No relevant systemic symptoms. The leg is involved. Symptoms reported: burning and itching. The patient considered this a rash. Present for one to four weeks. This image was taken at a distance. The contributor notes the lesion is rough or flaky:
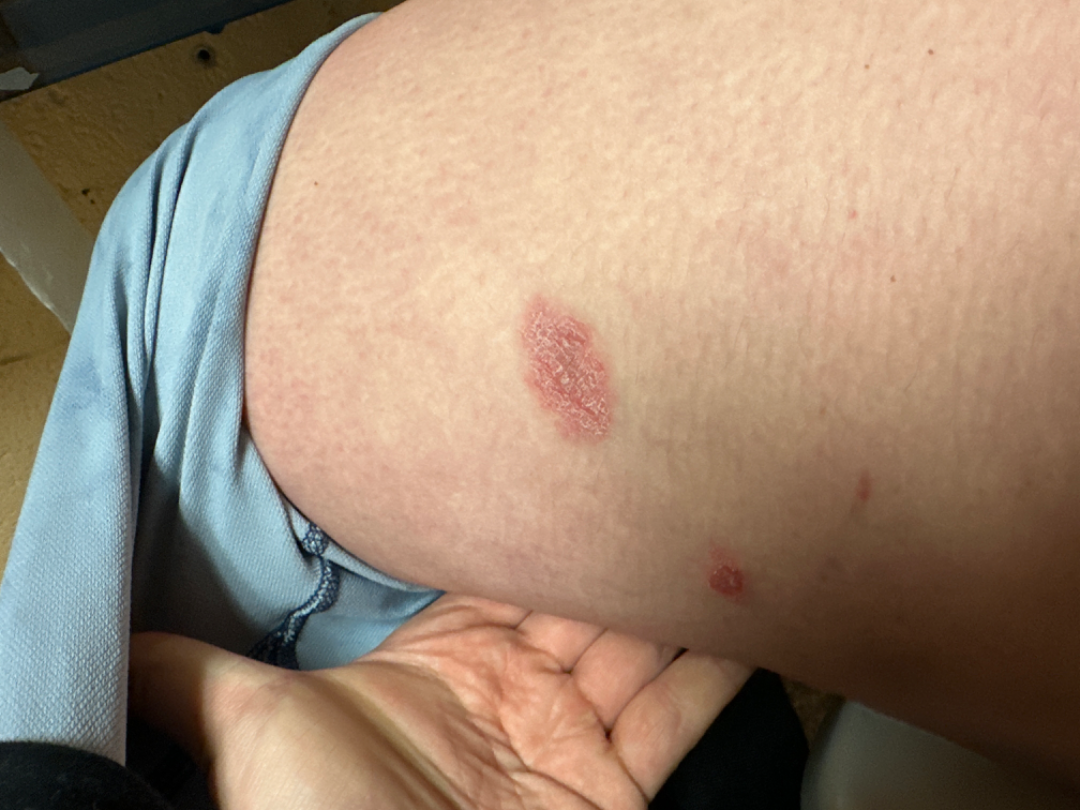Notes:
– assessment — ungradable on photographic review